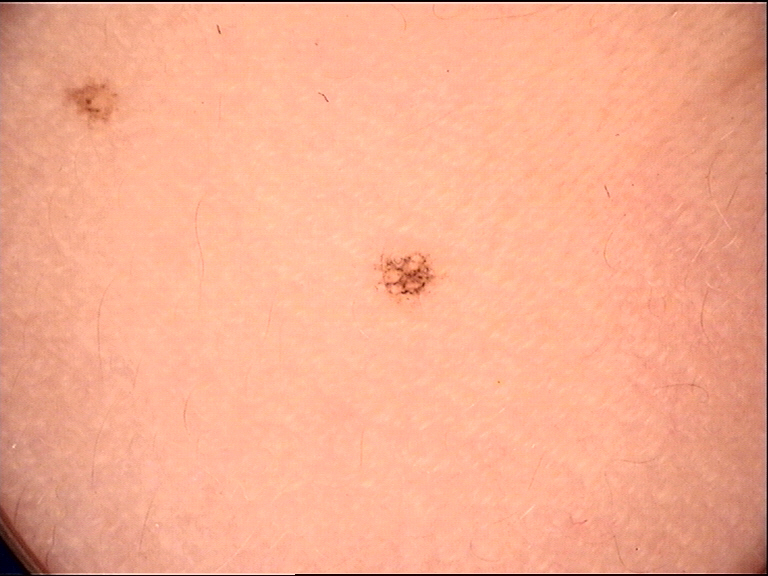The diagnosis was a benign lesion — a dysplastic junctional nevus.